The patient describes having few moles overall. The patient says their skin tans without first burning. A male patient 79 years of age:
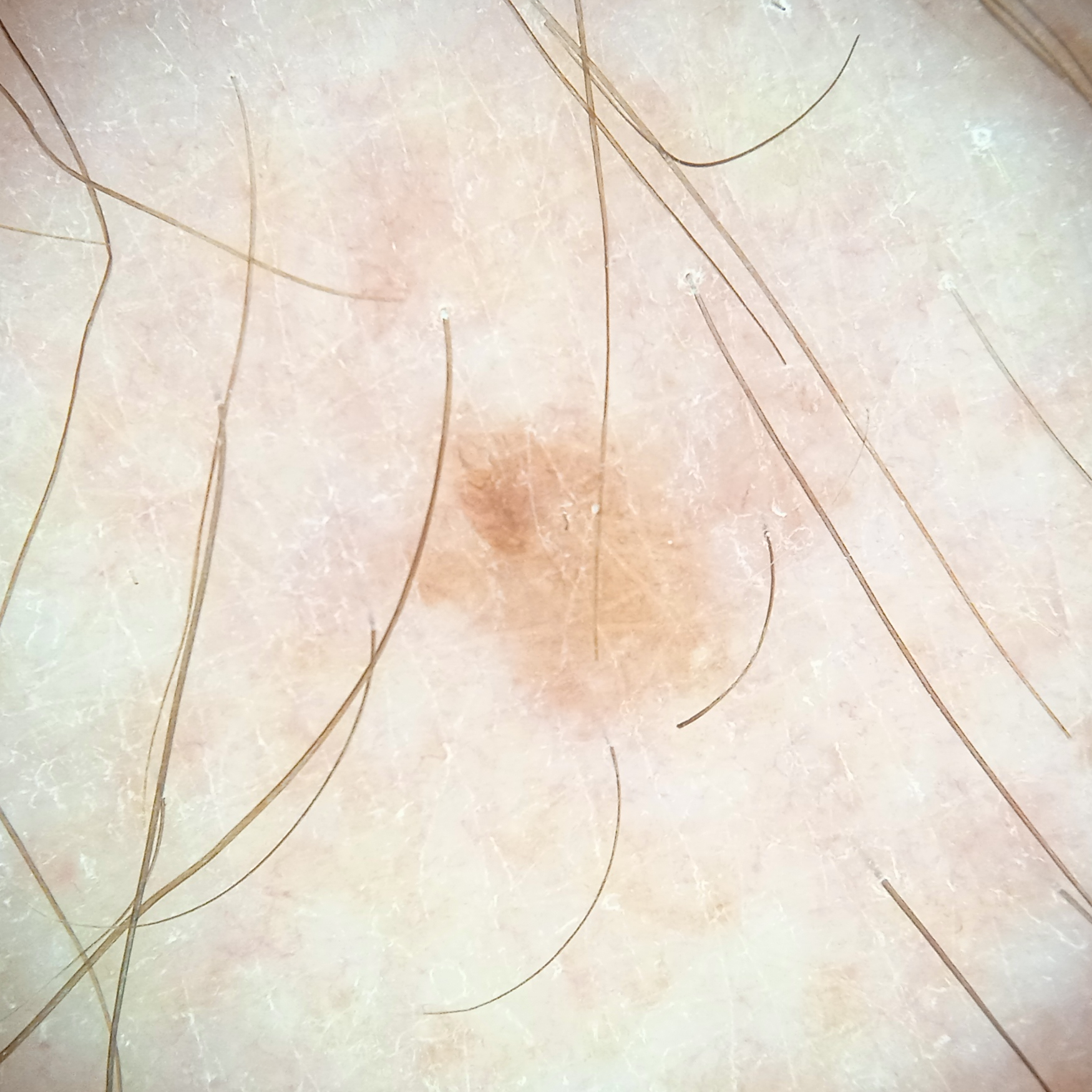The diagnostic impression was a seborrheic keratosis.